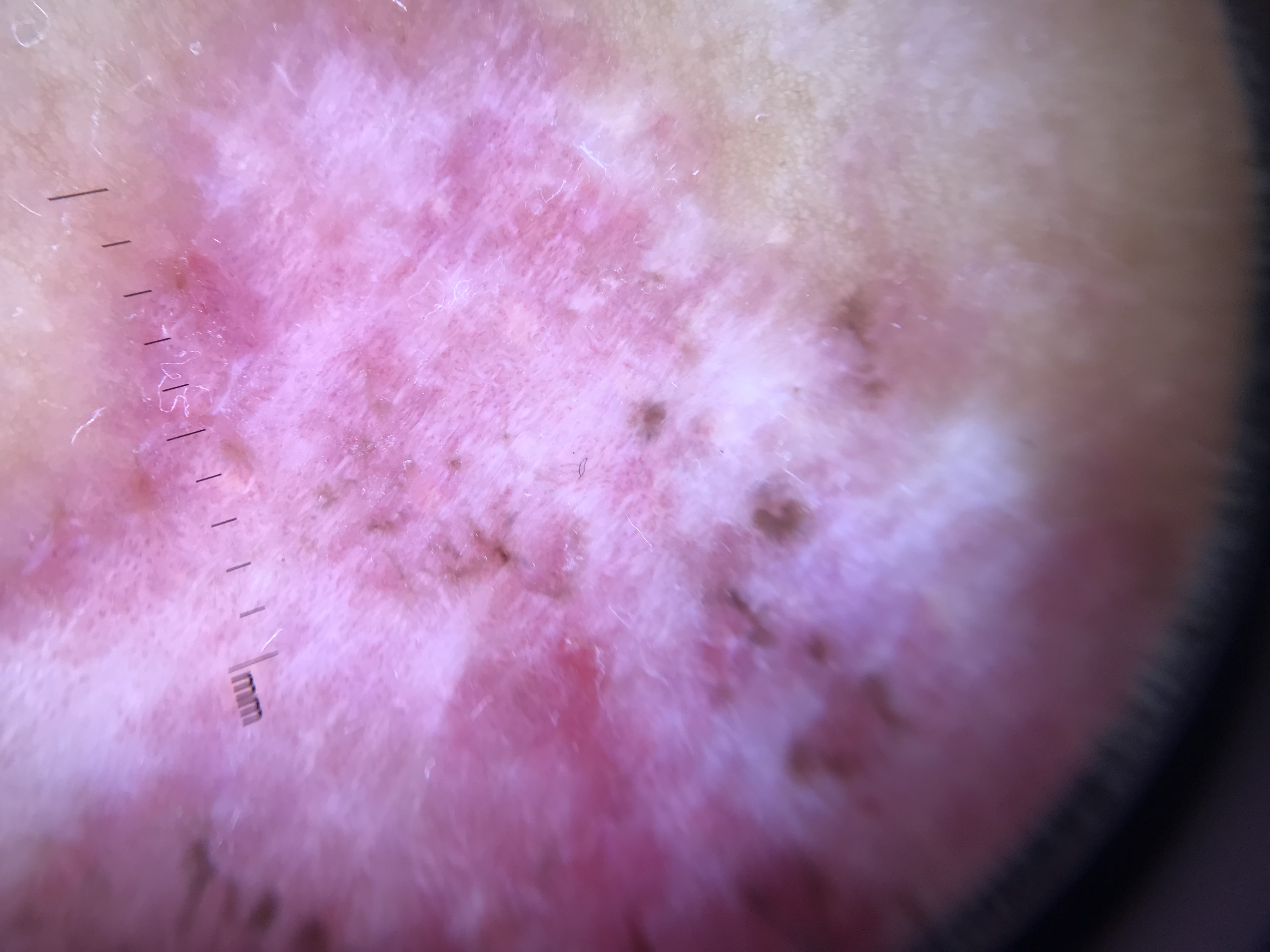Q: What is the diagnosis?
A: basal cell carcinoma (biopsy-proven)